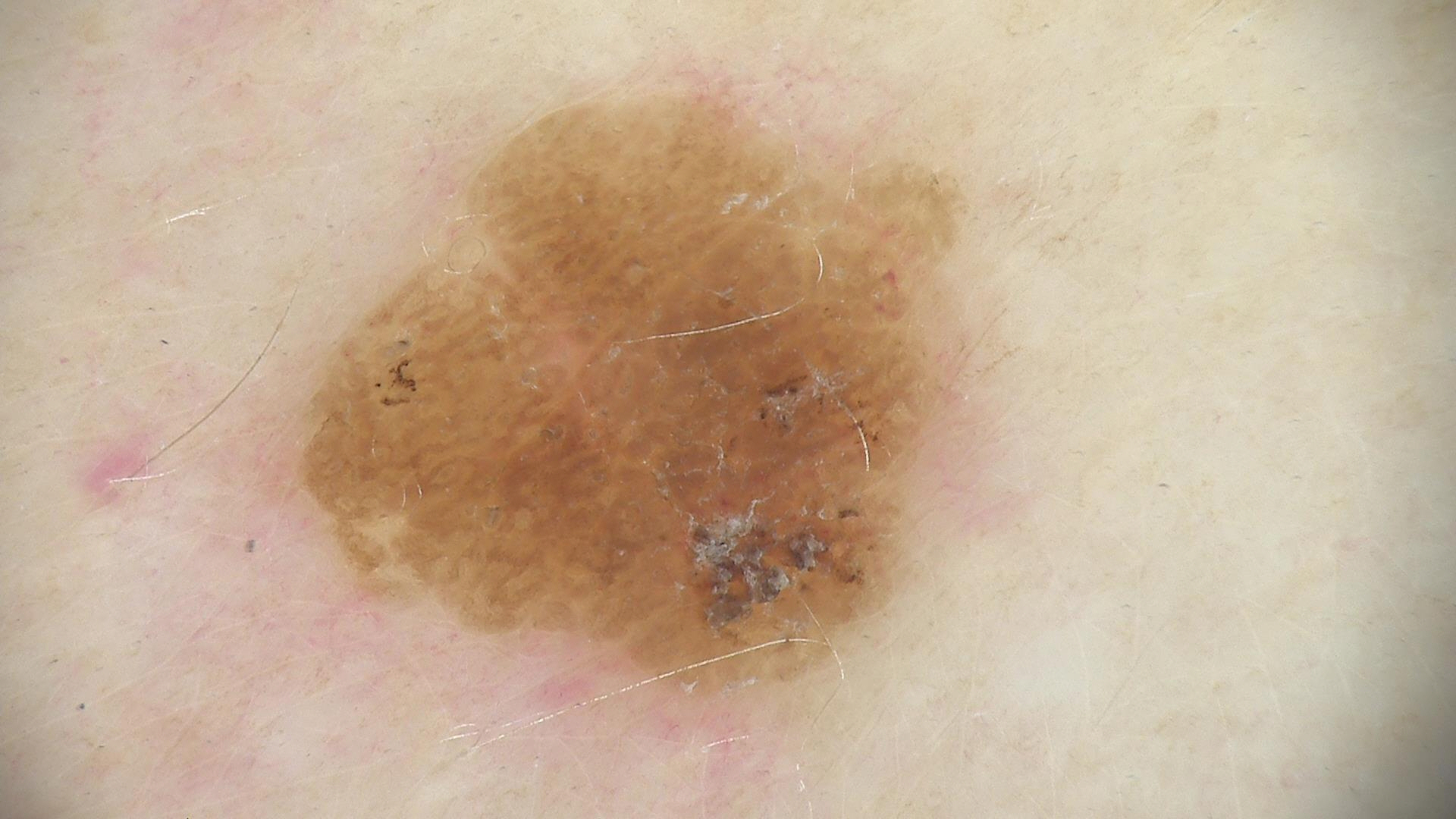diagnosis: seborrheic keratosis (expert consensus).